A dermoscopic image of a skin lesion.
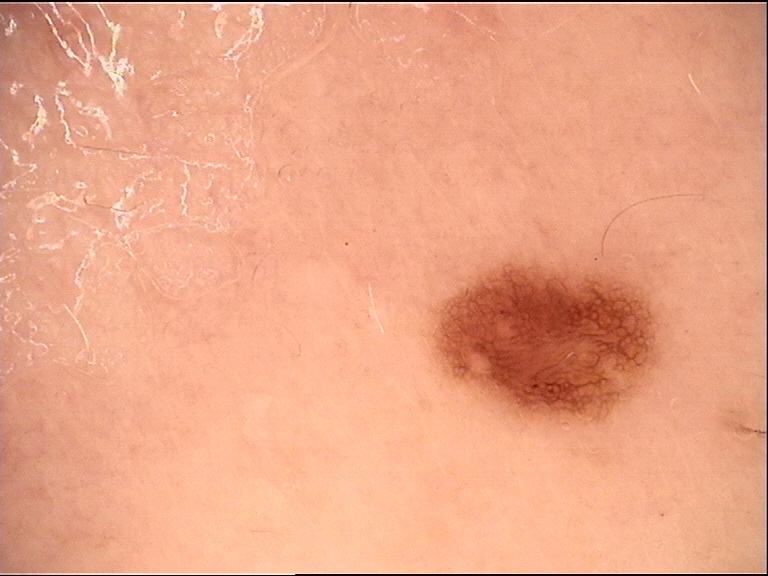The diagnosis was a benign lesion — a dysplastic junctional nevus.